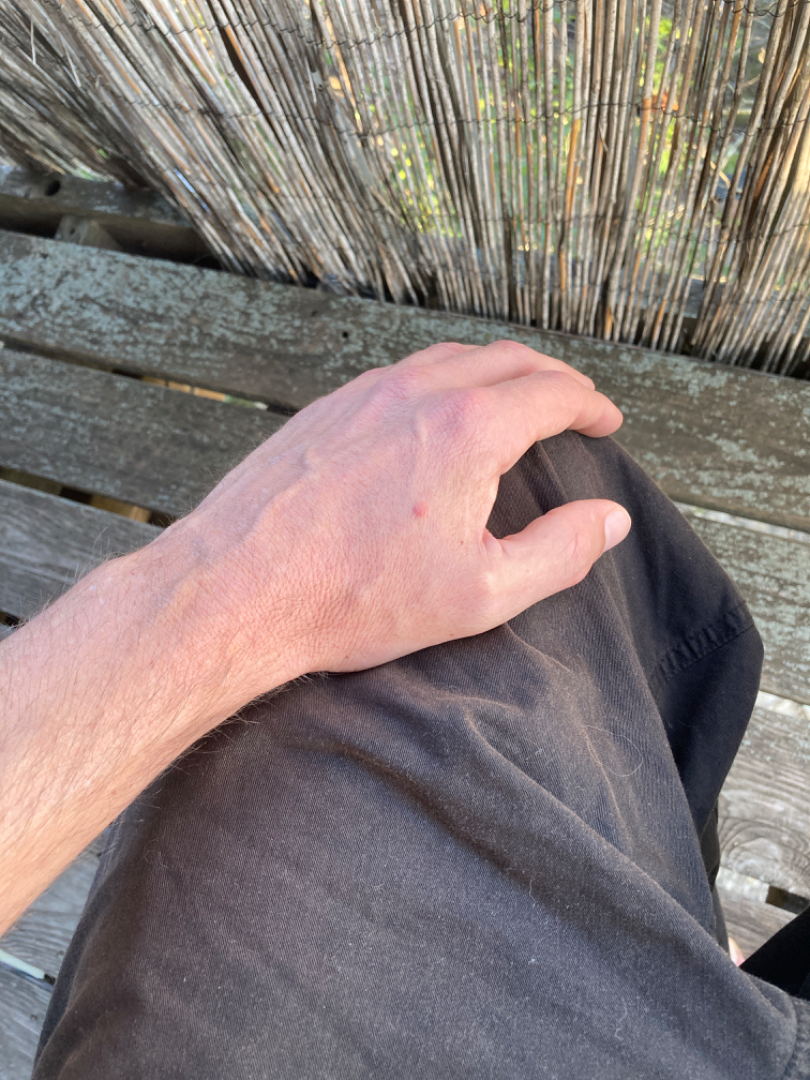Findings:
A single dermatologist reviewed the case: Melanocytic Nevus, SK/ISK and Verruca vulgaris were considered with similar weight.